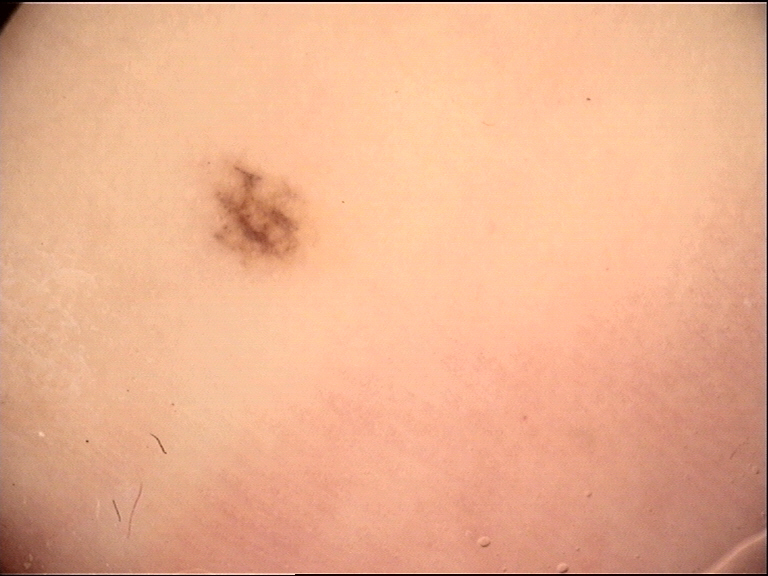The diagnostic label was an acral dysplastic junctional nevus.